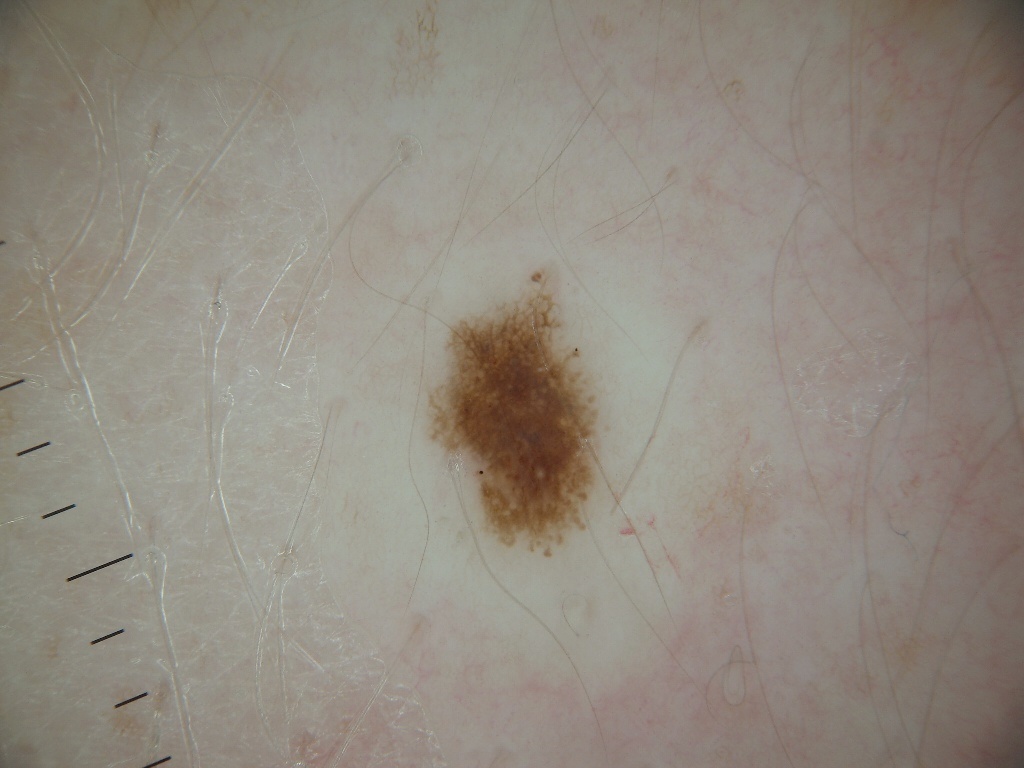Image and clinical context: Dermoscopy of a skin lesion. A female patient aged 38-42. In (x1, y1, x2, y2) order, the lesion is bounded by <bbox>421, 257, 614, 566</bbox>. The dermoscopic pattern shows globules, pigment network, and milia-like cysts. The lesion occupies roughly 6% of the field. Conclusion: The clinical diagnosis was a melanocytic nevus, a benign skin lesion.